A female subject aged around 20 · contact-polarized dermoscopy of a skin lesion.
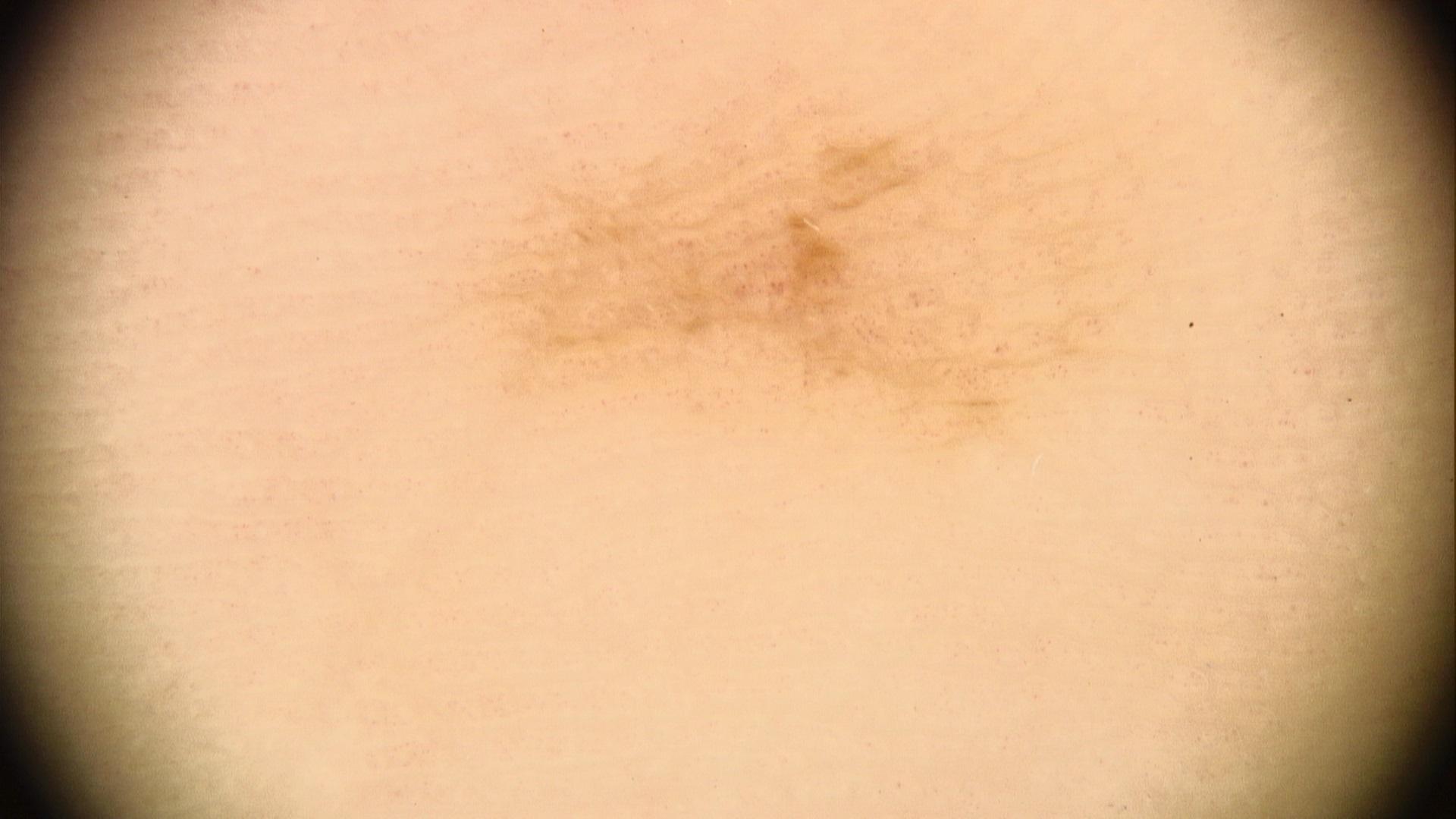Located on an acral site (palms or soles). The clinical impression was a nevus.